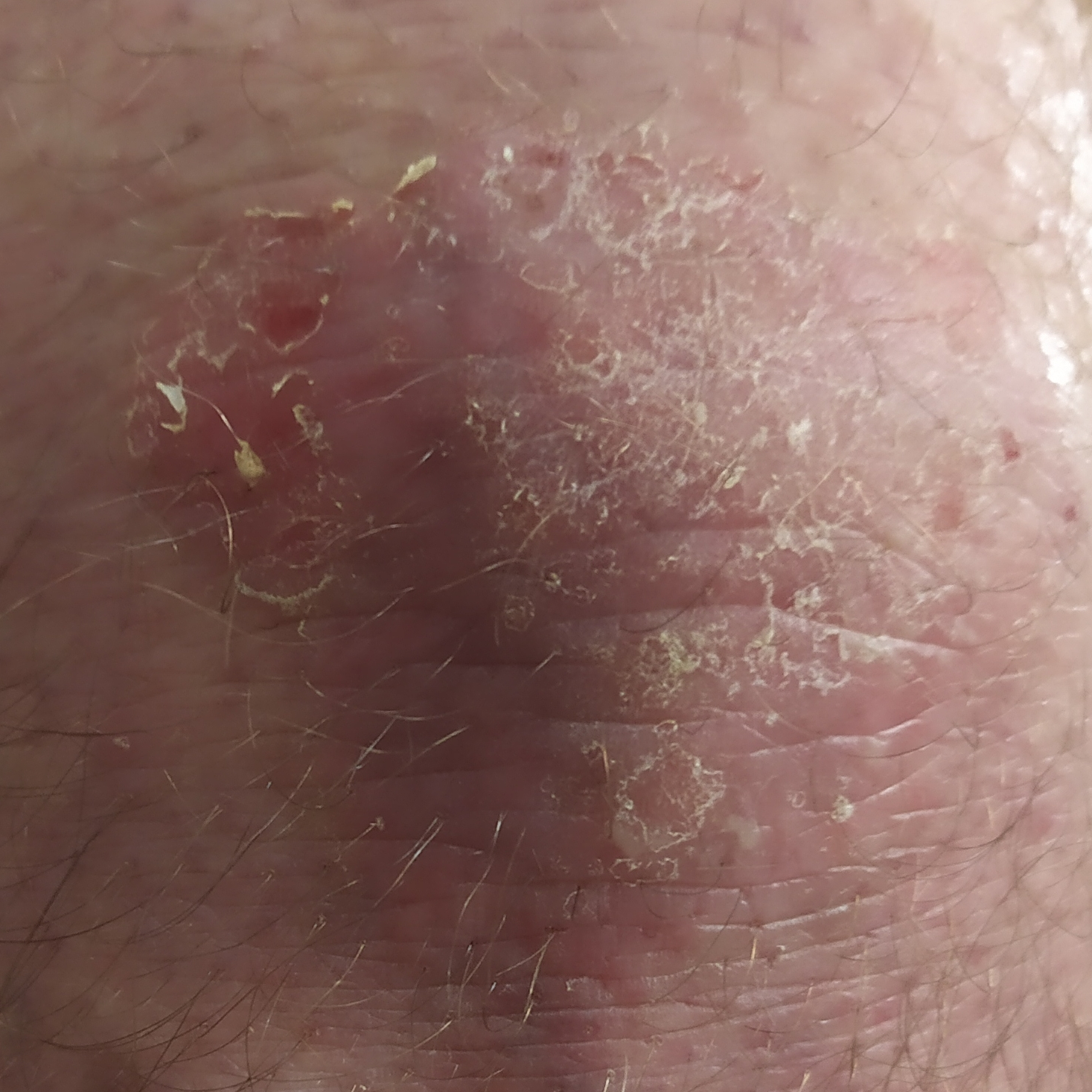Notes:
– subject: male, 51 years of age
– modality: clinical photo
– exposure history: prior malignancy (patient or family), alcohol use, pesticide exposure
– skin type: II
– size: 50 × 48 mm
– reported symptoms: itching
– diagnostic label: actinic keratosis (biopsy-proven)